This image was taken at a distance — 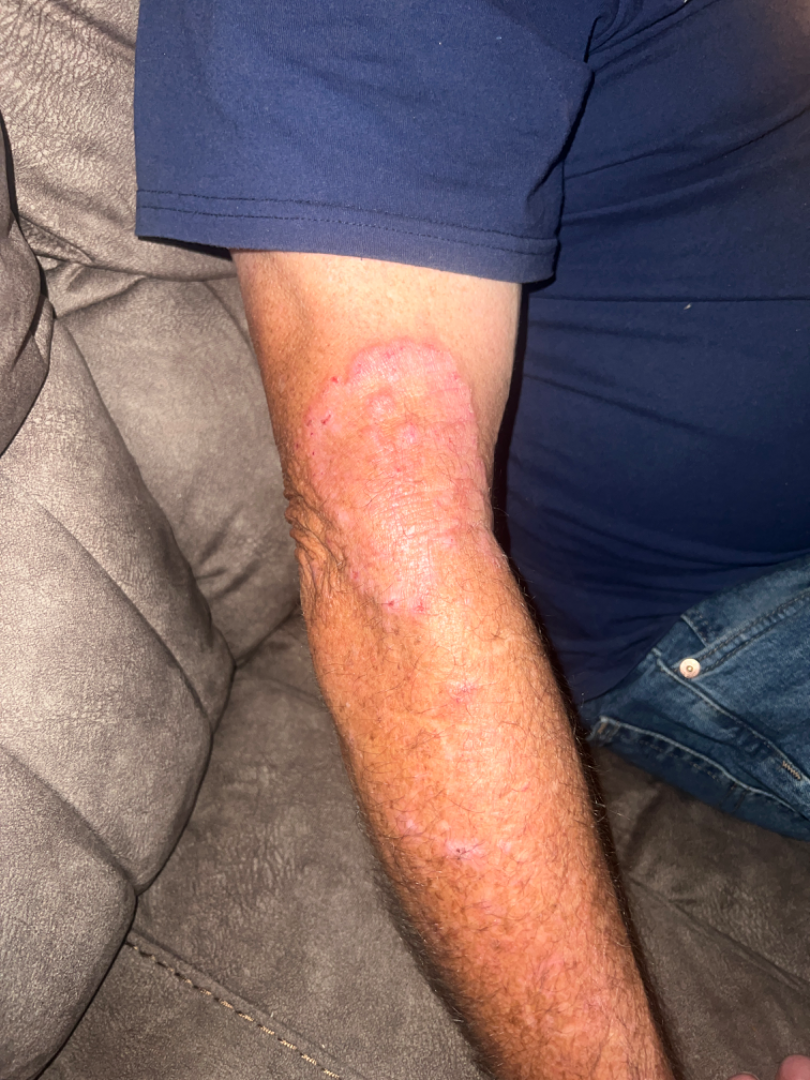A single dermatologist reviewed the case: the leading consideration is Tinea; also consider Granuloma annulare; an alternative is Psoriasis.